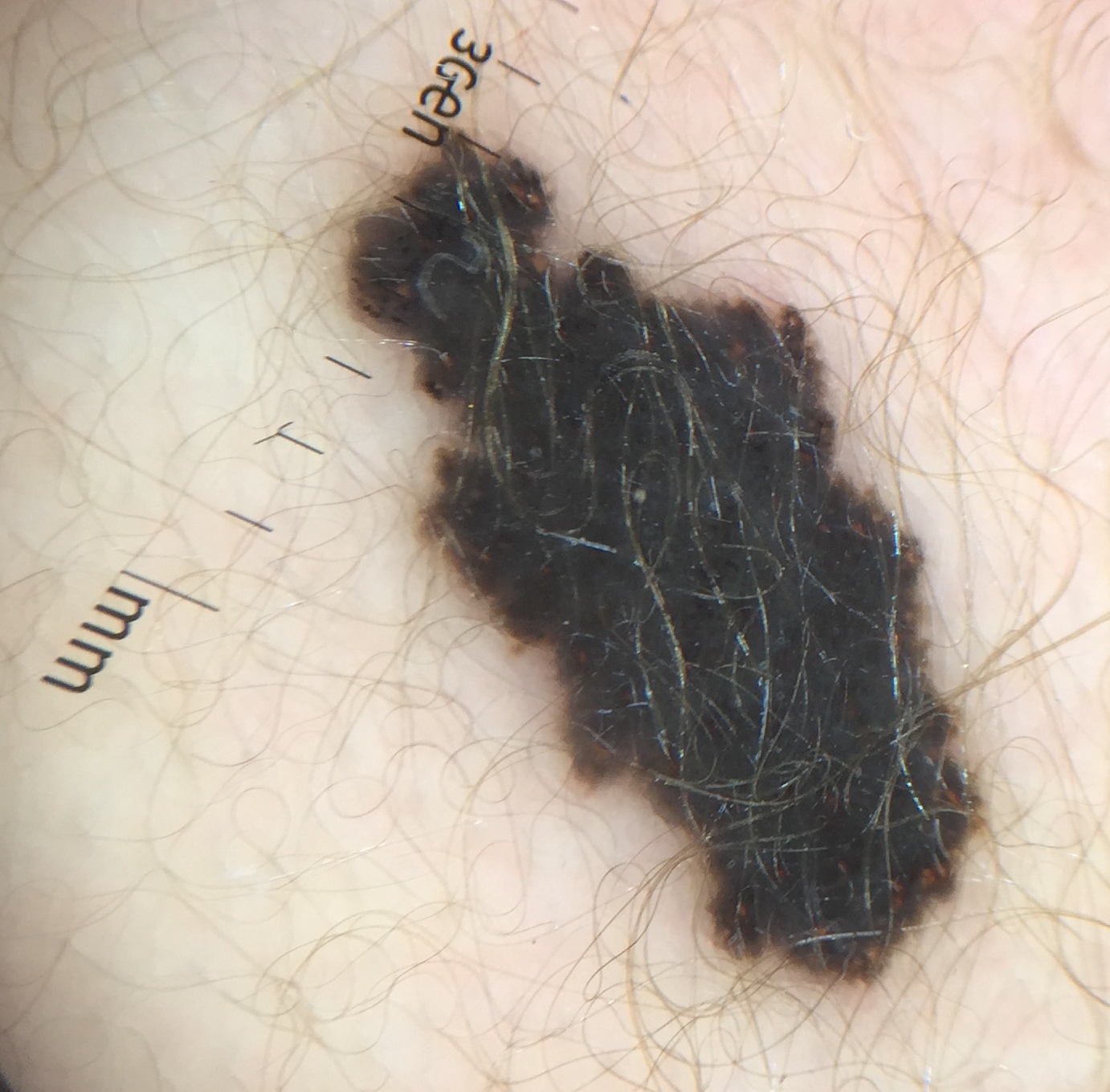Conclusion: Diagnosed as a congenital compound nevus.